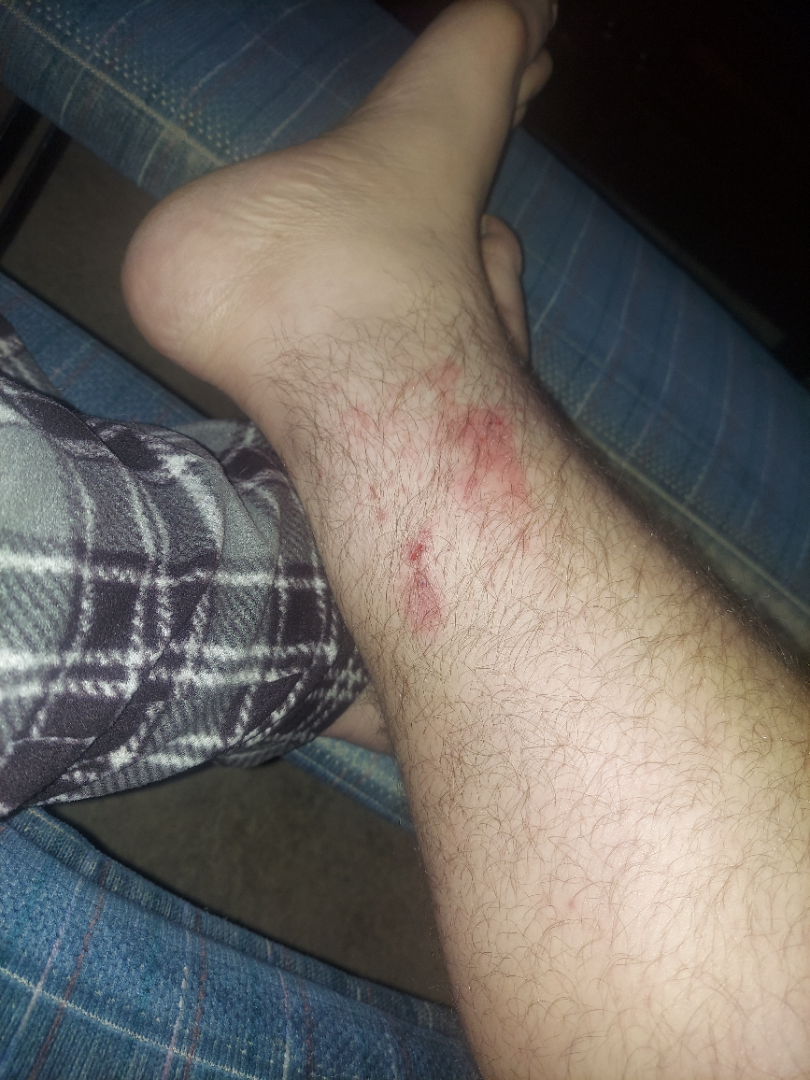view: at a distance
reported symptoms: bothersome appearance, itching and burning
lesion texture: rough or flaky
body site: leg
differential diagnosis: Eczema (0.41); Allergic Contact Dermatitis (0.41); Insect Bite (0.18)